The photo was captured at an angle: 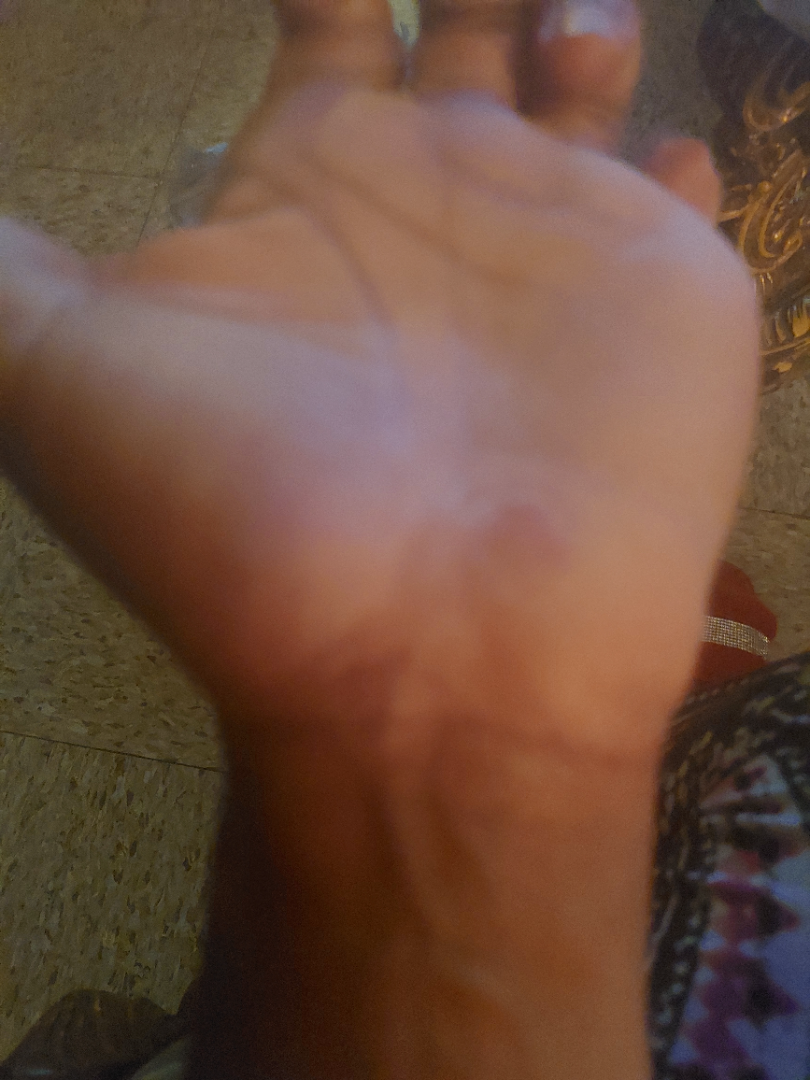Impression:
On teledermatology review: the differential, in no particular order, includes Psoriasis and Eczema; a remote consideration is Tinea.